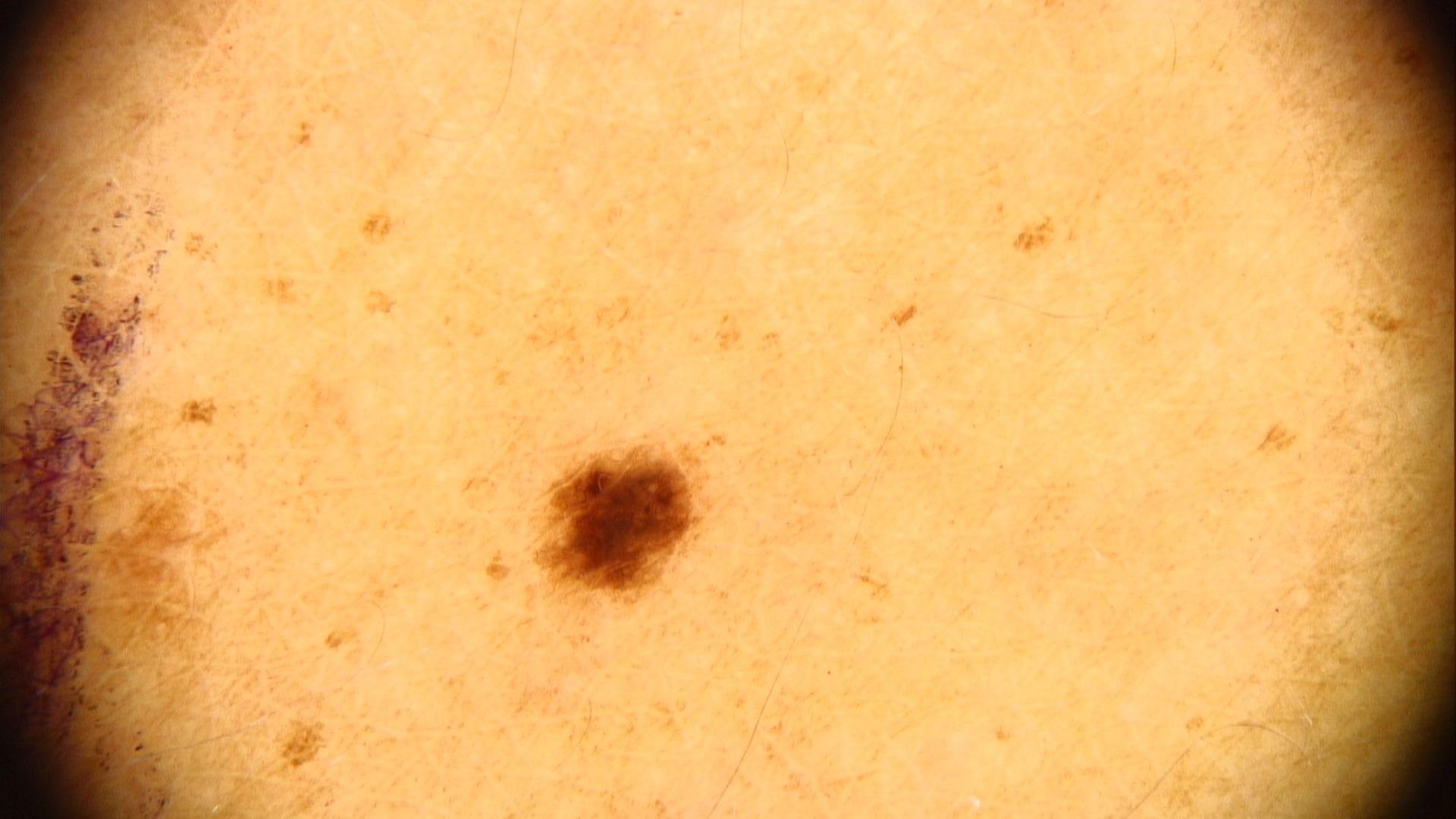| key | value |
|---|---|
| Fitzpatrick | III |
| subject | female, in their mid- to late 30s |
| relevant background | a first-degree relative with melanoma |
| image type | contact-polarized dermoscopy |
| diagnosis | Nevus (clinical impression) |